This image was taken at a distance; the leg is involved; female contributor, age 18–29.
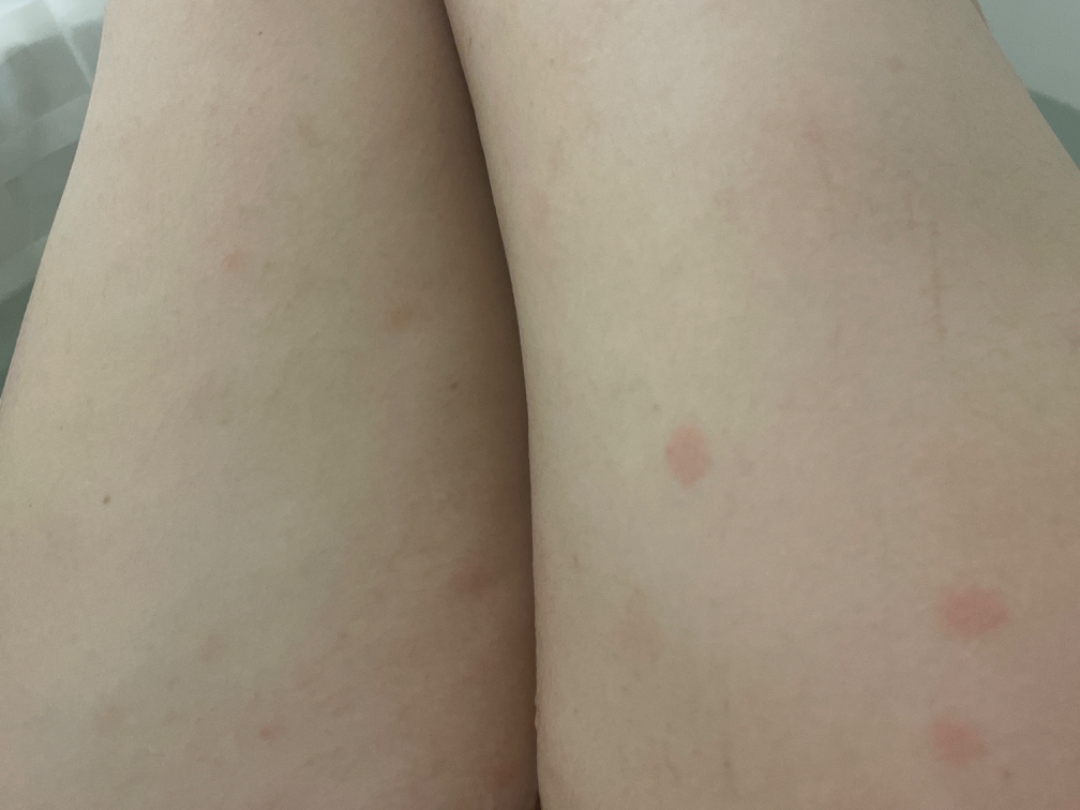Q: What conditions are considered?
A: Sweet syndrome (weight 0.33); Insect Bite (weight 0.33); Eczema (weight 0.33)